A dermoscopic close-up of a skin lesion · the patient is FST II · a male subject about 80 years old:
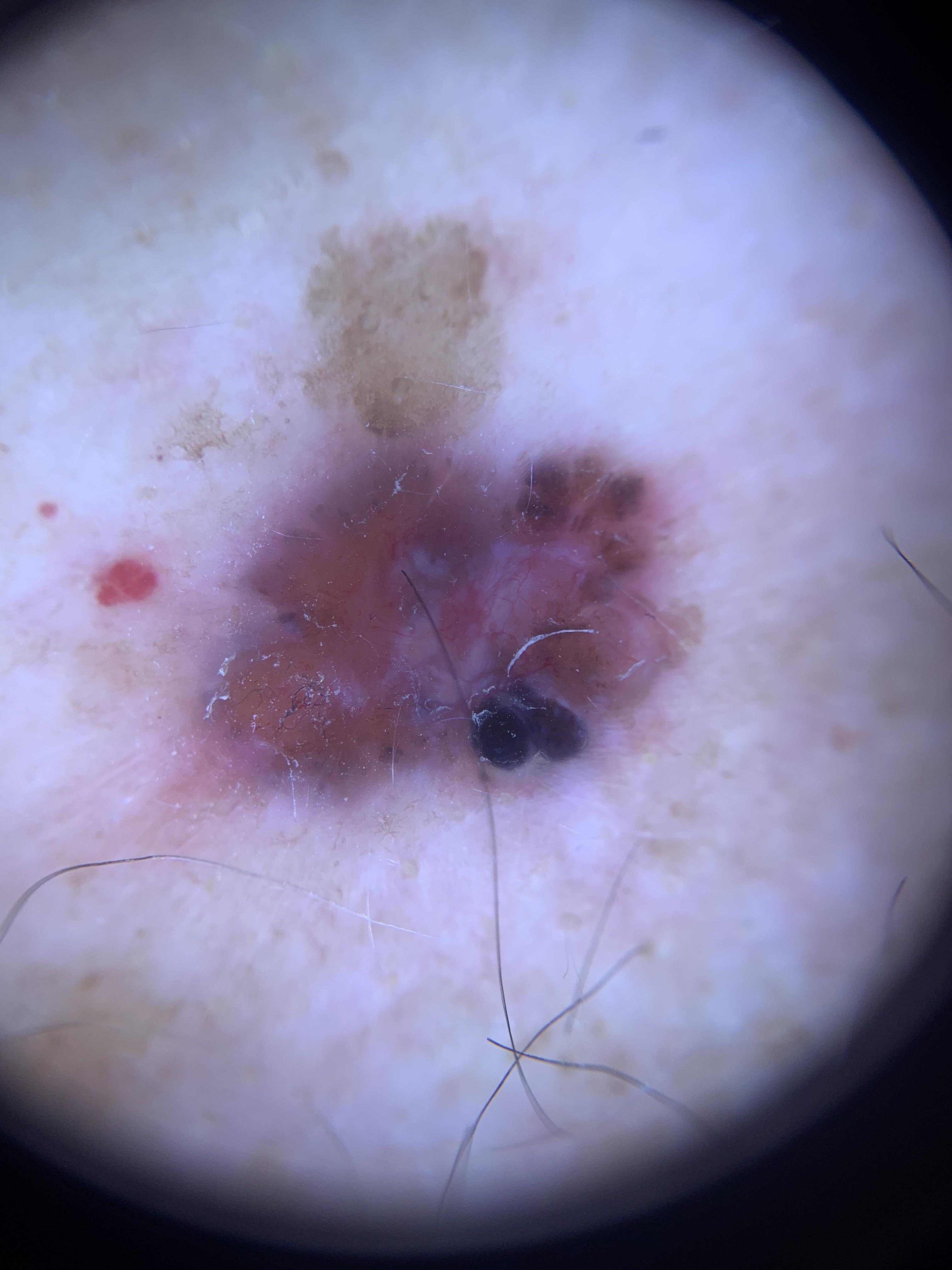The lesion is located on the trunk, specifically the anterior trunk.
Histopathologically confirmed as a malignant, adnexal lesion — a basal cell carcinoma.